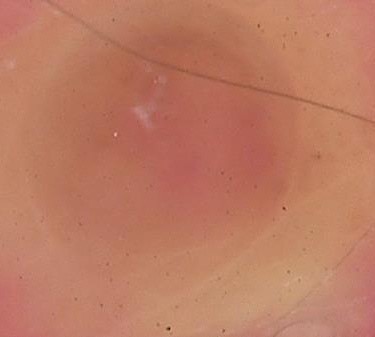{"diagnosis": {"name": "dermal nevus", "code": "db", "malignancy": "benign", "super_class": "melanocytic", "confirmation": "expert consensus"}}